Dermoscopy of a skin lesion.
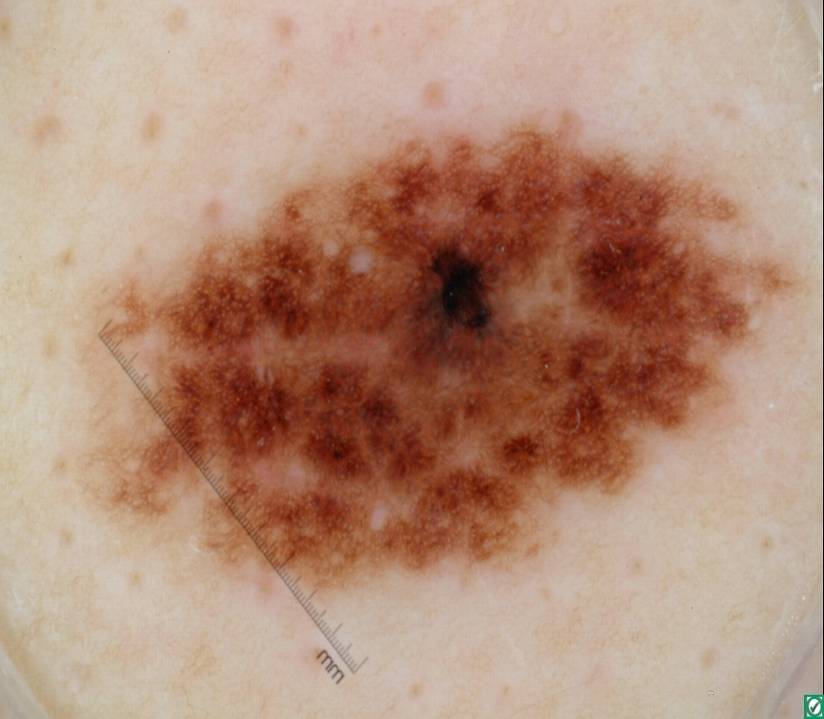In (x1, y1, x2, y2) order, the lesion occupies the region (98, 110, 792, 601). Dermoscopic assessment notes pigment network, with no streaks, globules, milia-like cysts, or negative network. The lesion takes up a large portion of the image. On biopsy, the diagnosis was a melanoma, a skin cancer.